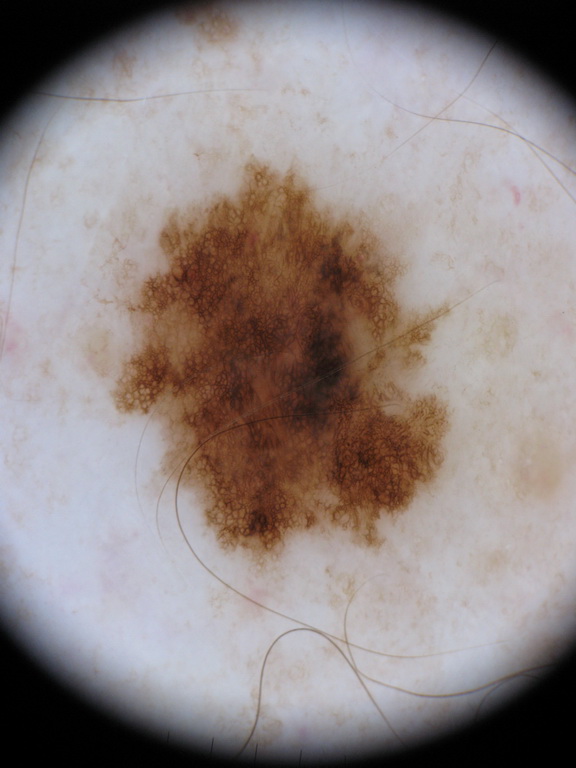Q: Patient demographics?
A: male, aged 73-77
Q: What is the imaging modality?
A: dermoscopic image
Q: Where is the lesion in the image?
A: [112, 160, 449, 563]
Q: What dermoscopic features are present?
A: pigment network; absent: globules, negative network, streaks, and milia-like cysts
Q: How much of the field does the lesion occupy?
A: ~21% of the field
Q: What is this lesion?
A: a melanocytic nevus, a benign lesion